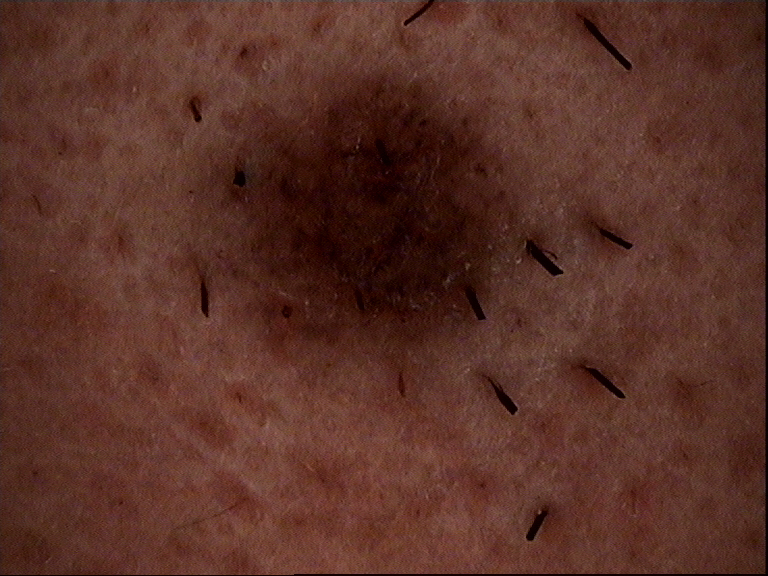imaging: dermoscopy | subtype: banal | class: compound nevus (expert consensus).